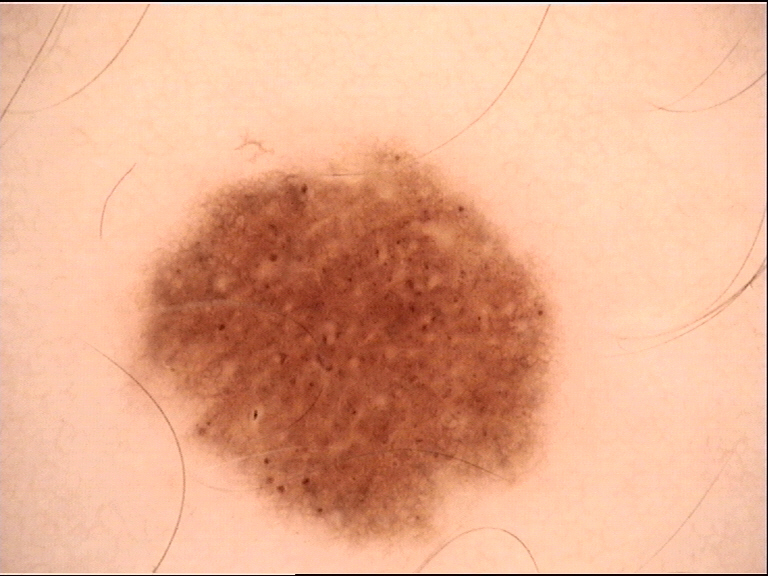image type=dermoscopy | diagnostic label=dysplastic junctional nevus (expert consensus).